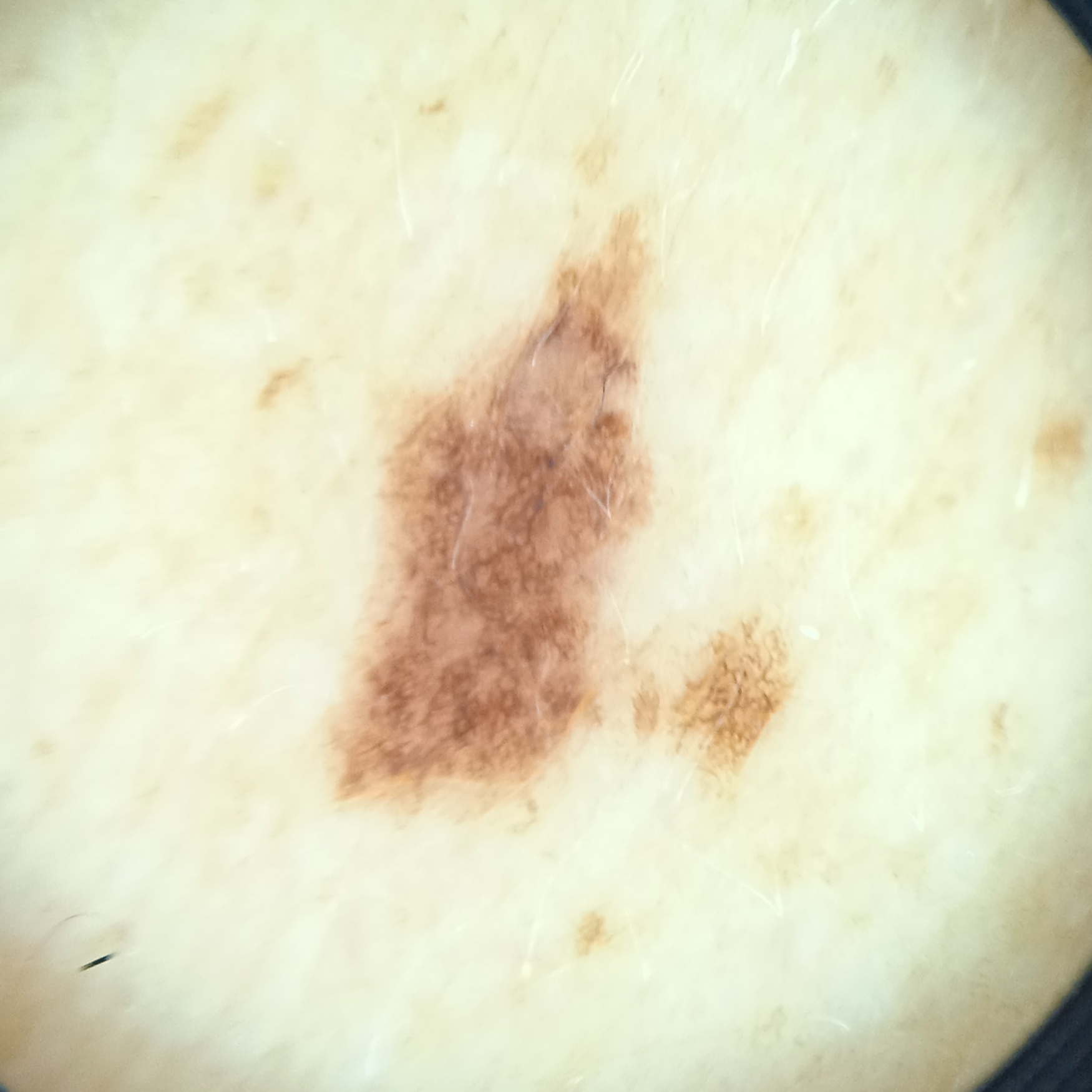diagnosis: atypical (dysplastic) nevus — biopsy-proven.